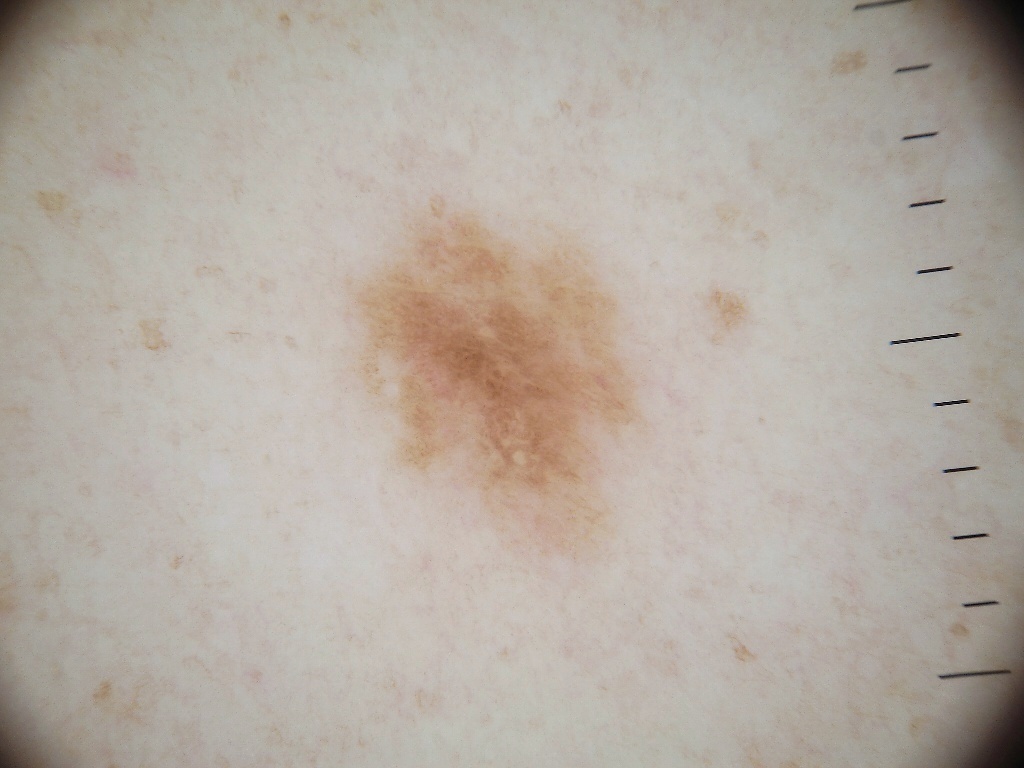patient: female, aged 43-47; image: dermoscopy; features: negative network; lesion location: <box>342, 192, 654, 563</box>; size: ~10% of the field; diagnosis: a melanocytic nevus, a benign skin lesion.